Reported duration is more than one year · located on the top or side of the foot and leg · the patient reported no systemic symptoms · texture is reported as rough or flaky and raised or bumpy · the patient reports bothersome appearance, burning, itching and darkening · the photograph was taken at an angle: 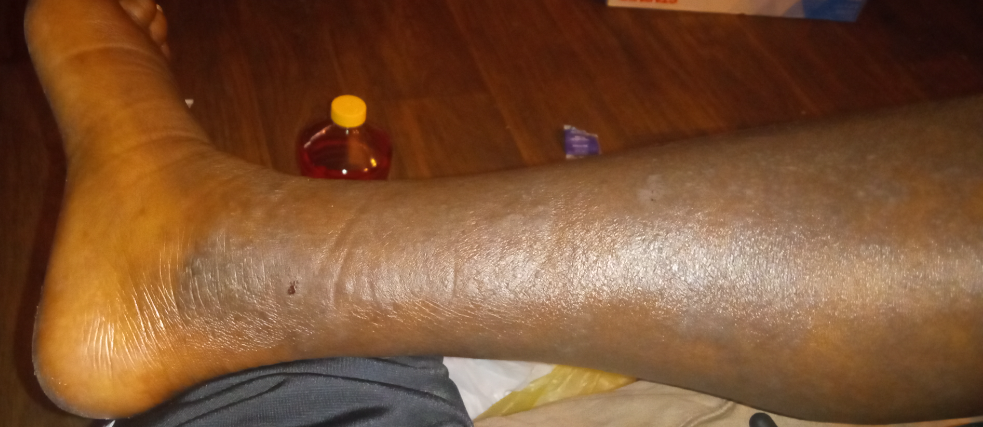| feature | finding |
|---|---|
| impression | the differential, in no particular order, includes Stasis Dermatitis; Eczema; and Contact dermatitis, NOS |